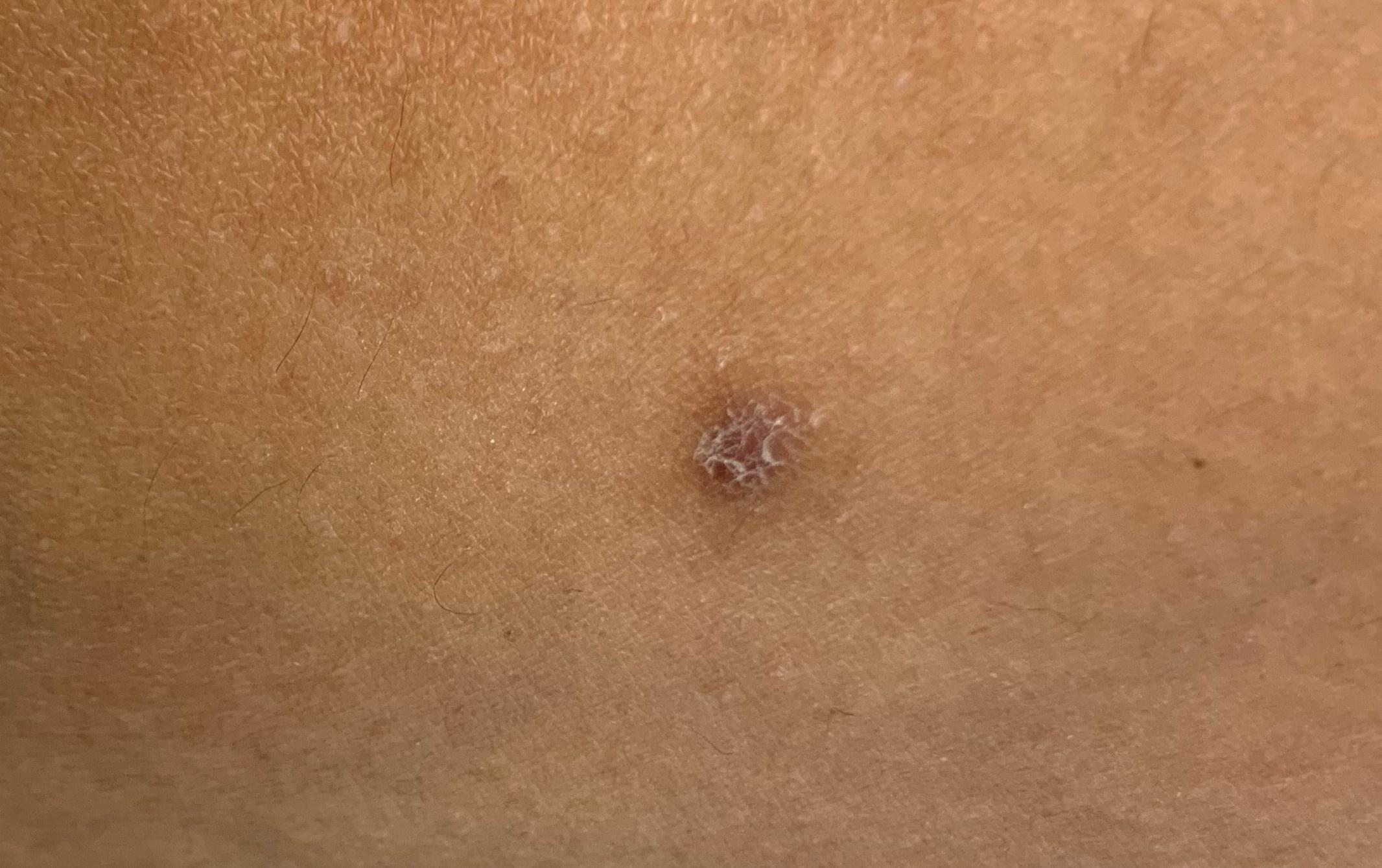{"patient": {"age_approx": 45, "sex": "female"}, "lesion_location": {"region": "a lower extremity"}, "diagnosis": {"name": "Dermatofibroma", "malignancy": "benign", "confirmation": "expert clinical impression", "lineage": "fibro-histiocytic"}}